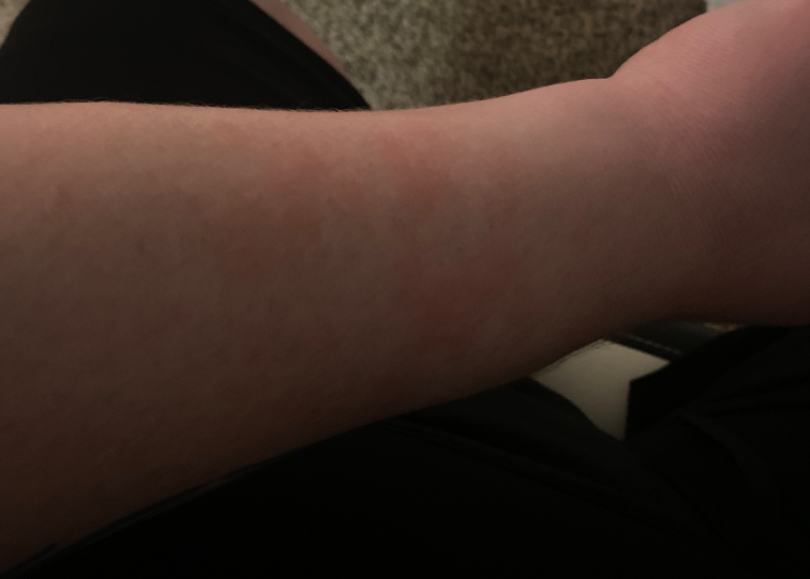| key | value |
|---|---|
| image framing | close-up |
| symptom duration | less than one week |
| surface texture | raised or bumpy and flat |
| anatomic site | arm |
| patient's own categorization | a rash |
| dermatologist impression | most likely Urticaria; an alternative is Eczema |